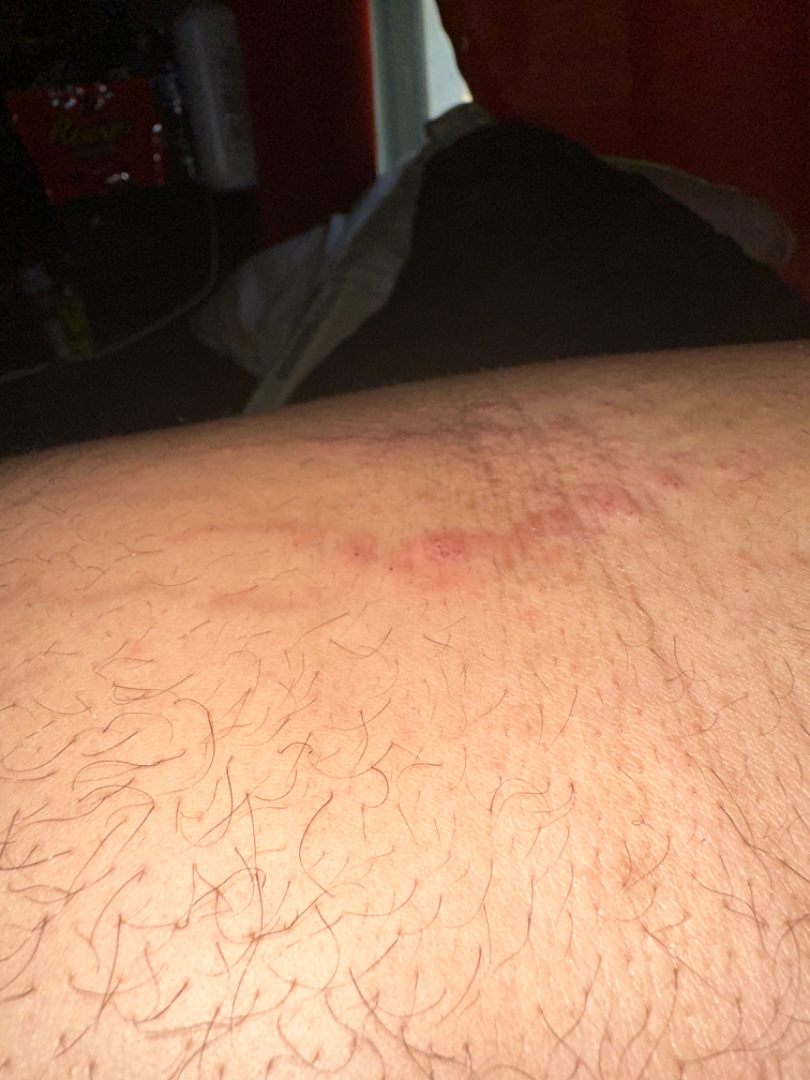Assessment:
The dermatologist could not determine a likely condition from the photograph alone.
Clinical context:
The patient indicates bothersome appearance, itching and pain. Self-categorized by the patient as a rash. The patient indicates the lesion is raised or bumpy and rough or flaky. The photograph was taken at an angle. The condition has been present for less than one week.